The patient considered this a rash, close-up view, the contributor is a male aged 18–29, Fitzpatrick phototype II, the arm is involved.
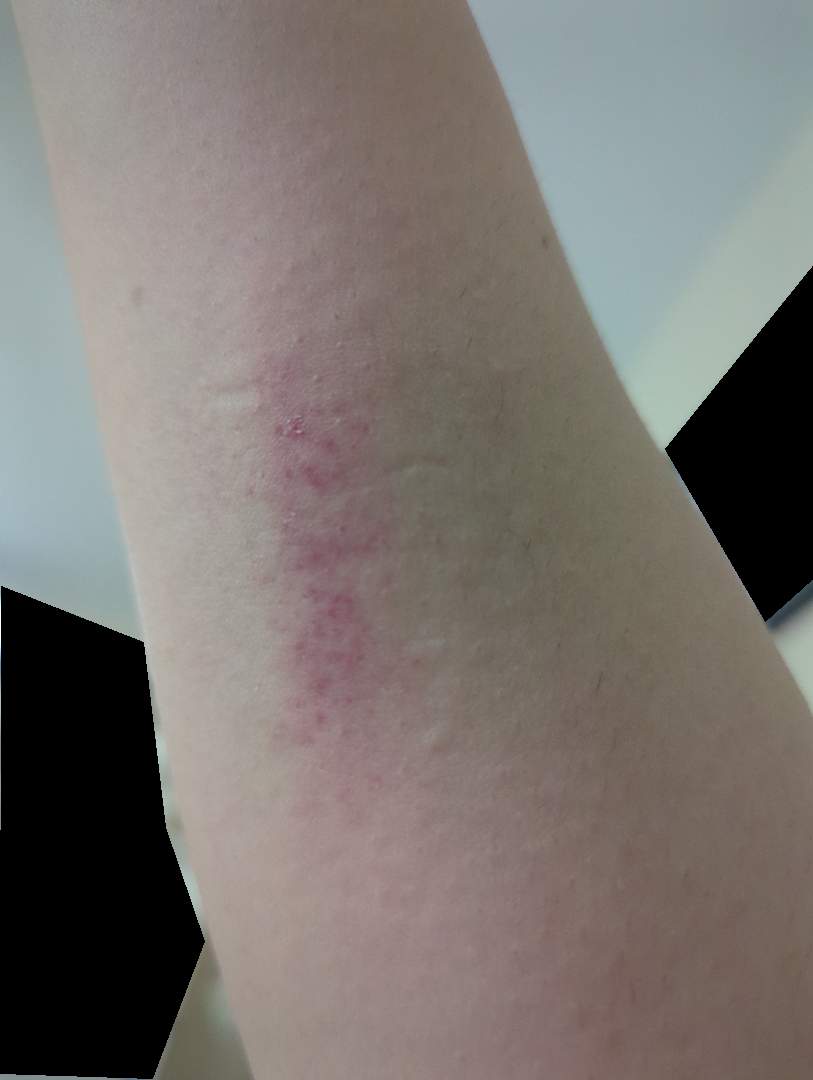Assessment:
The differential, in no particular order, includes Irritant Contact Dermatitis; Abrasion, scrape, or scab; Contact dermatitis; and Eczema; less likely is Allergic Contact Dermatitis.